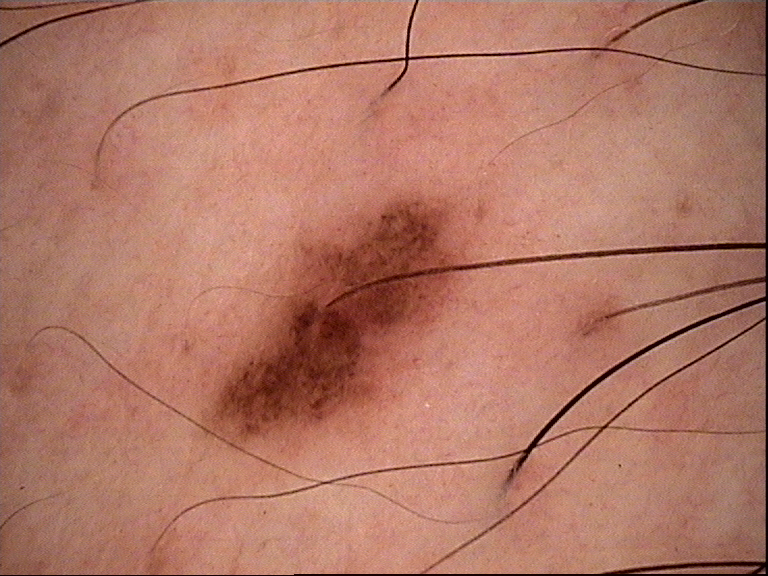A dermoscopic photograph of a skin lesion. The diagnostic label was a benign lesion — a dysplastic junctional nevus.